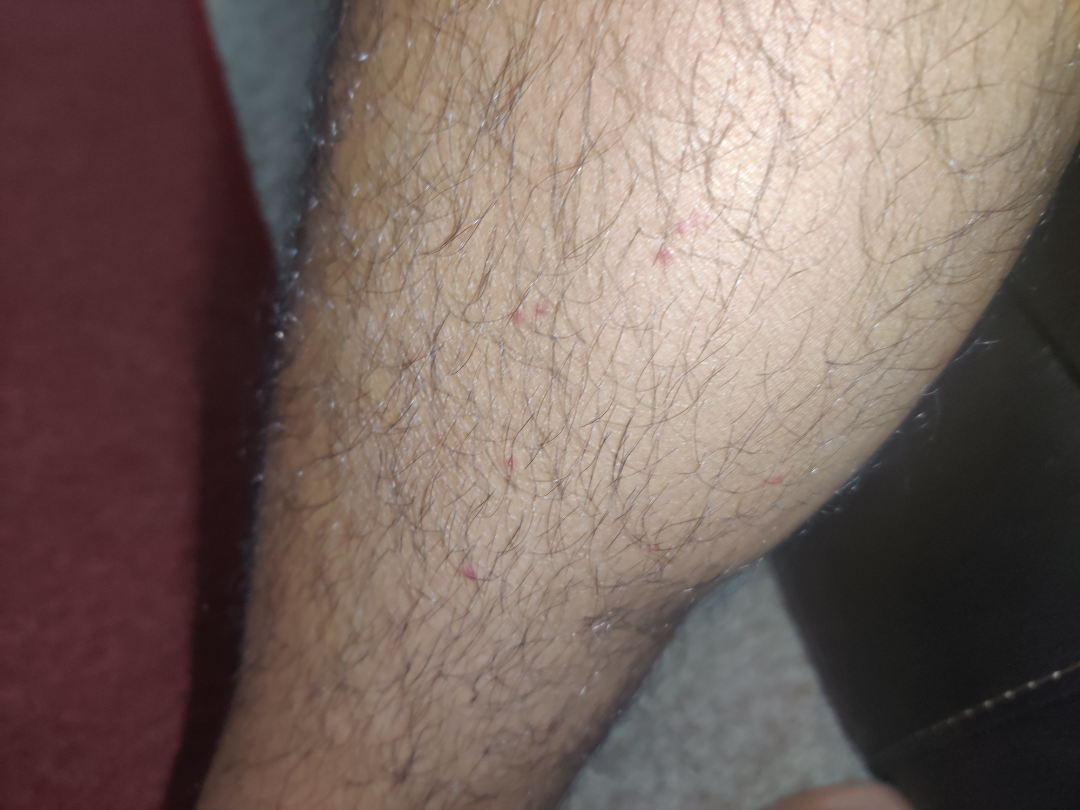Assessment:
The dermatologist could not determine a likely condition from the photograph alone.
Clinical context:
Male patient, age 18–29. The photo was captured at an angle. The lesion involves the arm and leg.